Skin tone: Fitzpatrick phototype V; the photo was captured at a distance.
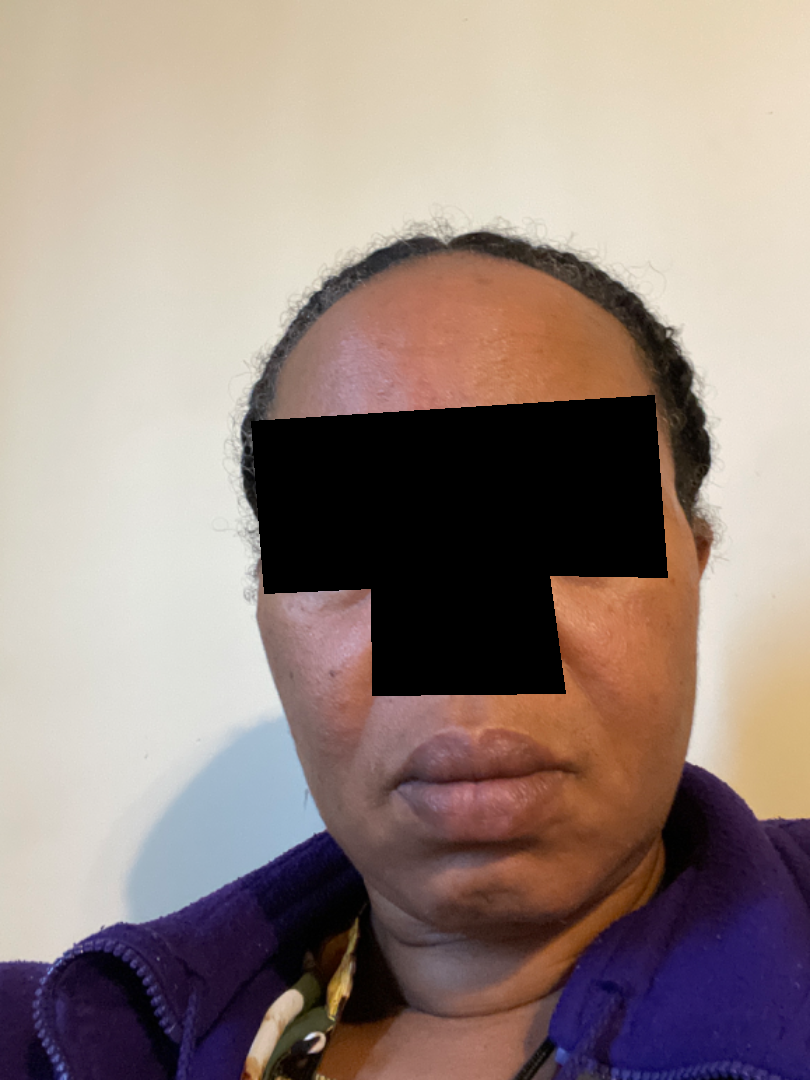The reviewing dermatologist was unable to assign a differential diagnosis from the image.